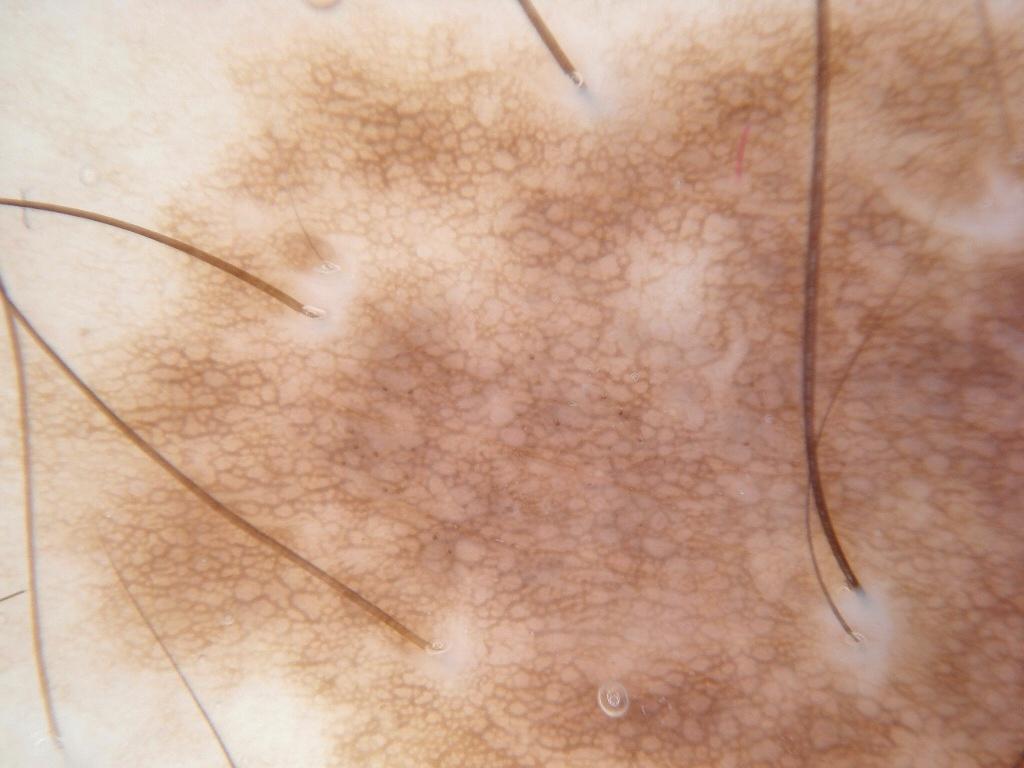{
  "patient": {
    "sex": "male",
    "age_approx": 40
  },
  "image": {
    "modality": "dermoscopy"
  },
  "lesion_location": "spans the dermoscopic field",
  "dermoscopic_features": {
    "present": [
      "pigment network"
    ],
    "absent": [
      "milia-like cysts",
      "streaks",
      "negative network"
    ]
  },
  "diagnosis": {
    "name": "melanocytic nevus",
    "malignancy": "benign",
    "lineage": "melanocytic",
    "provenance": "clinical"
  }
}